This image was taken at a distance · the contributor is a female aged 40–49 · the affected area is the top or side of the foot, sole of the foot and leg:
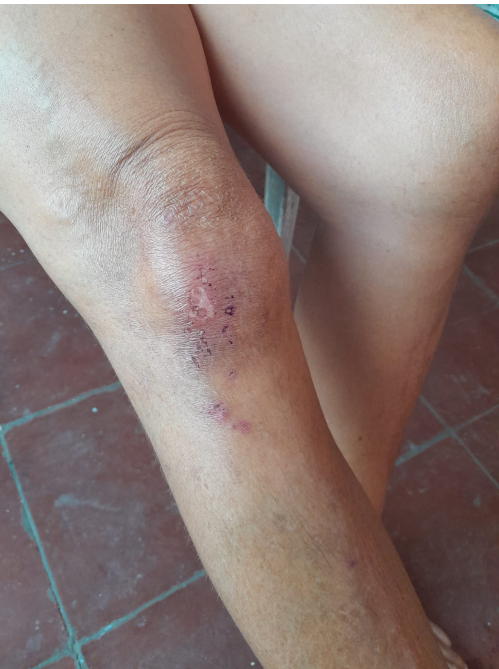Q: What is the differential diagnosis?
A: most consistent with Lichen Simplex Chronicus